Dermoscopy of a skin lesion.
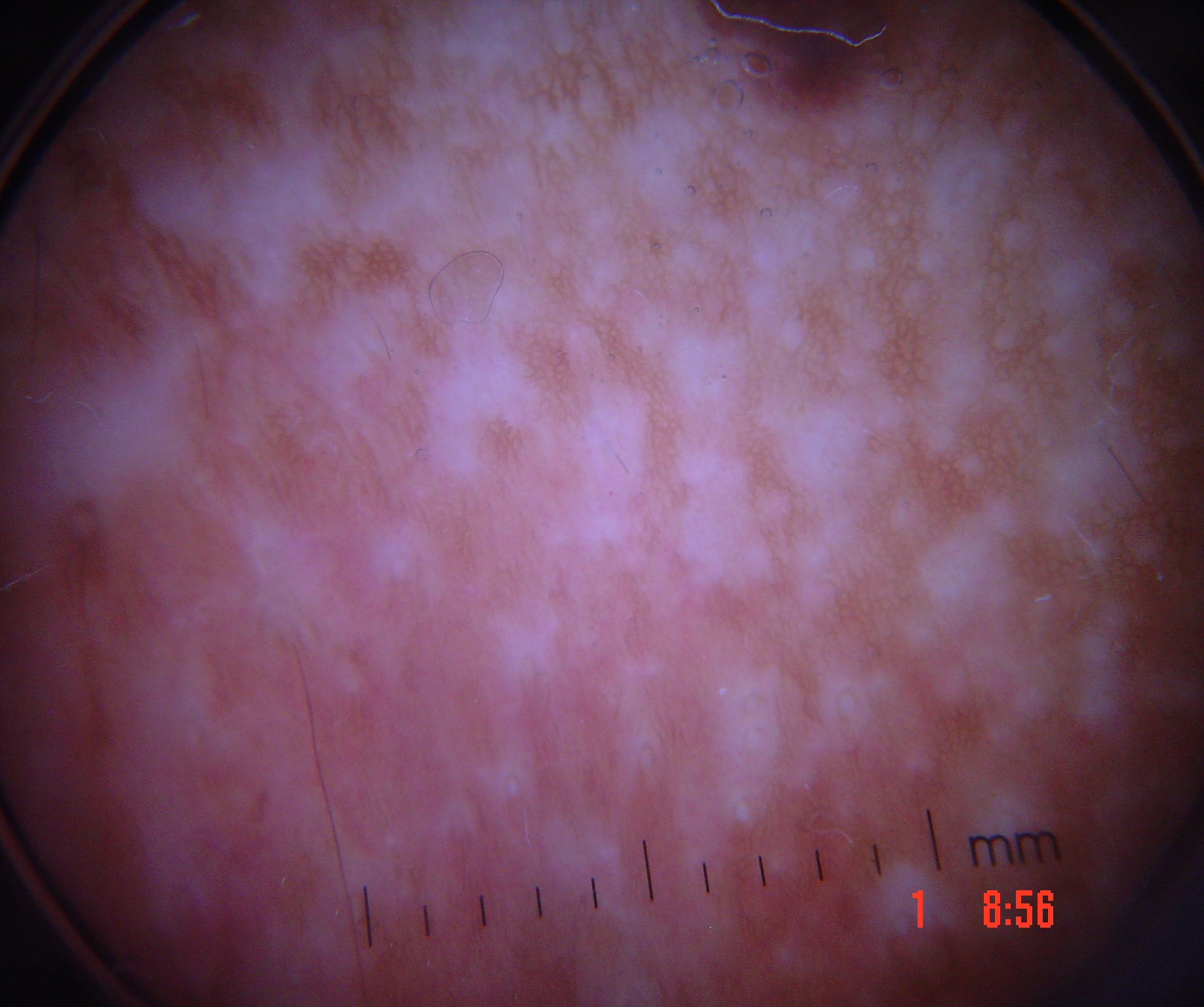Labeled as a benign lesion — a dysplastic junctional nevus.